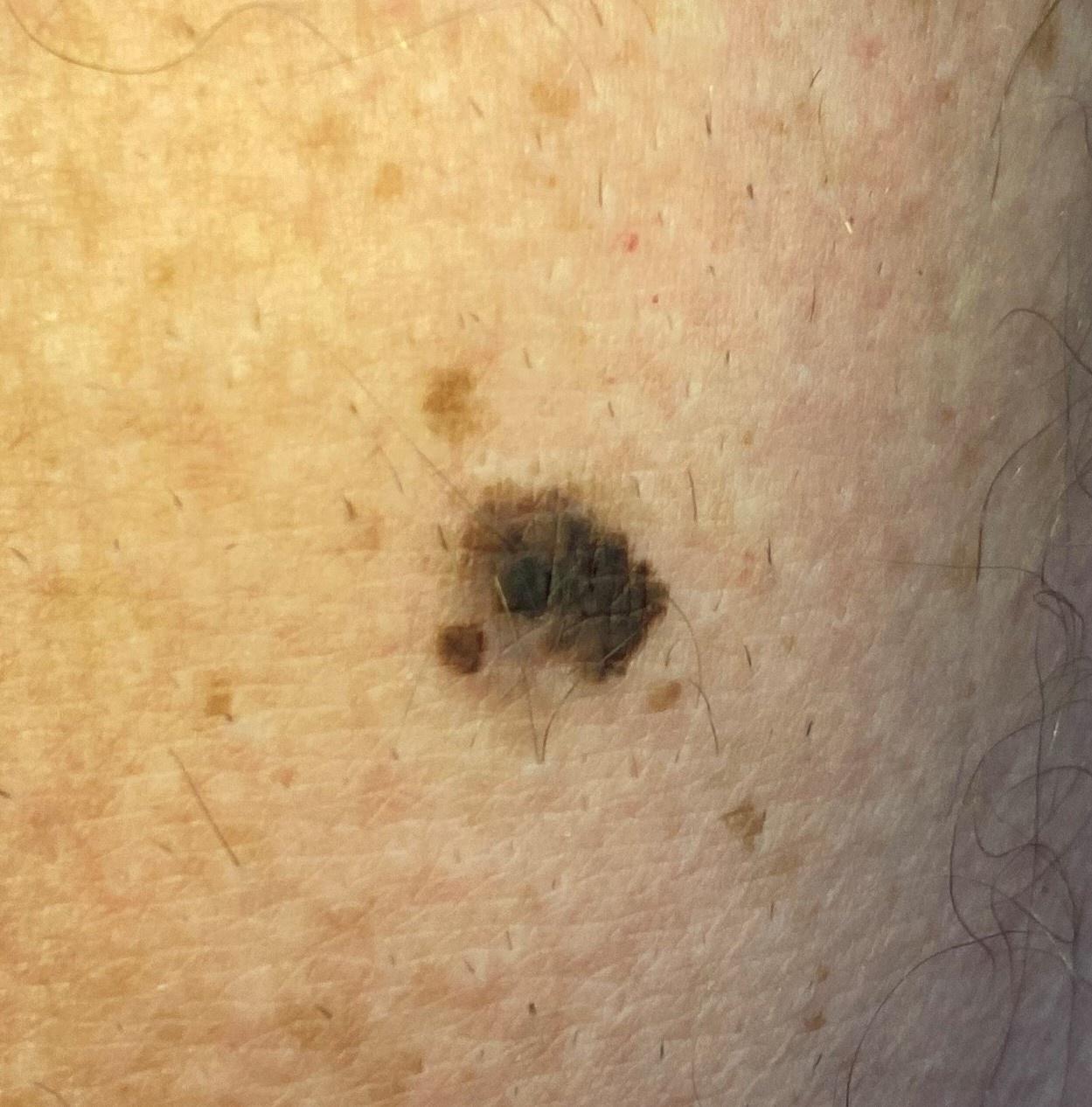{
  "image": "clinical overview photograph",
  "patient": {
    "age_approx": 60,
    "sex": "male"
  },
  "lesion_location": {
    "region": "an upper extremity"
  },
  "diagnosis": {
    "name": "Melanoma",
    "malignancy": "malignant",
    "confirmation": "histopathology"
  }
}